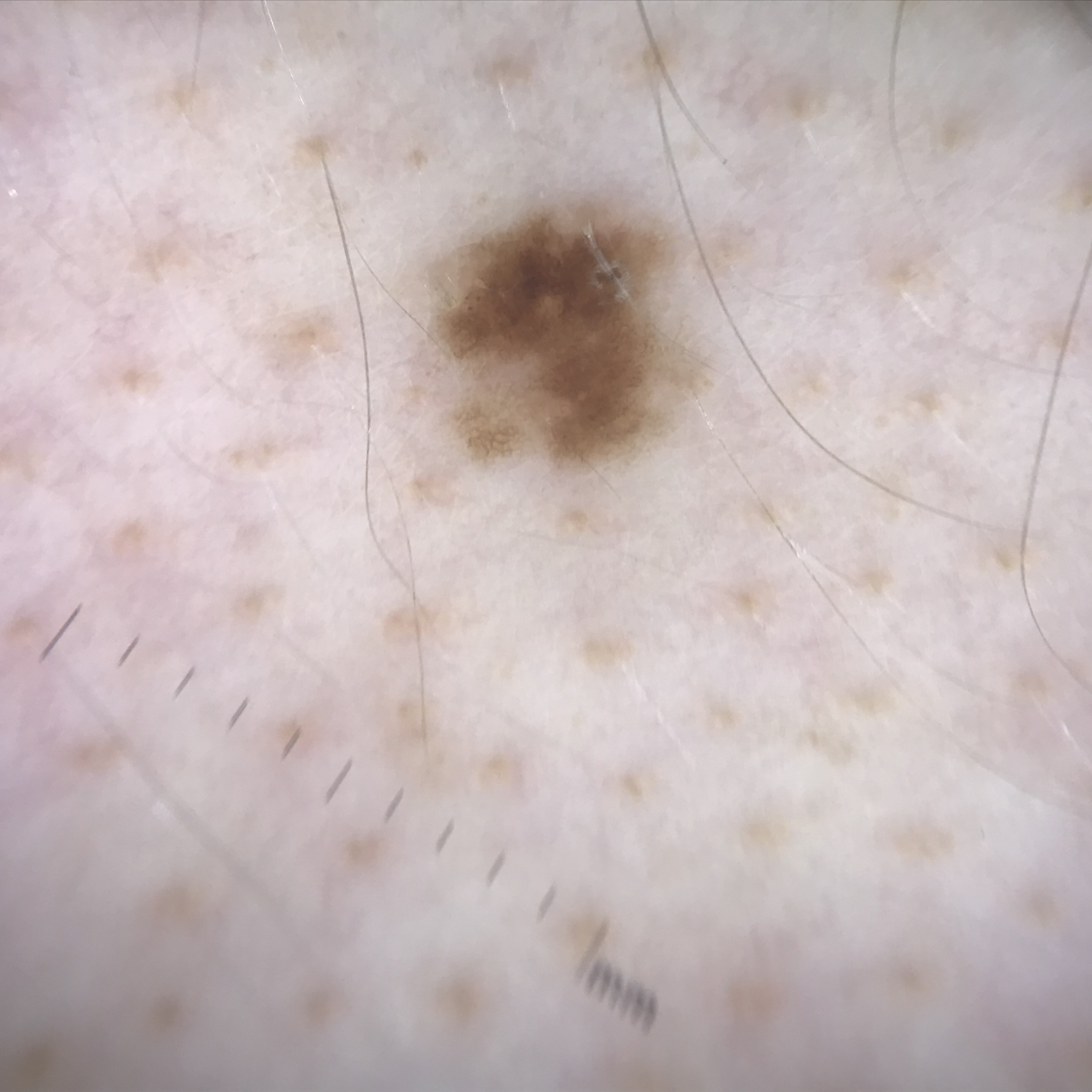Diagnosed as a dysplastic junctional nevus.